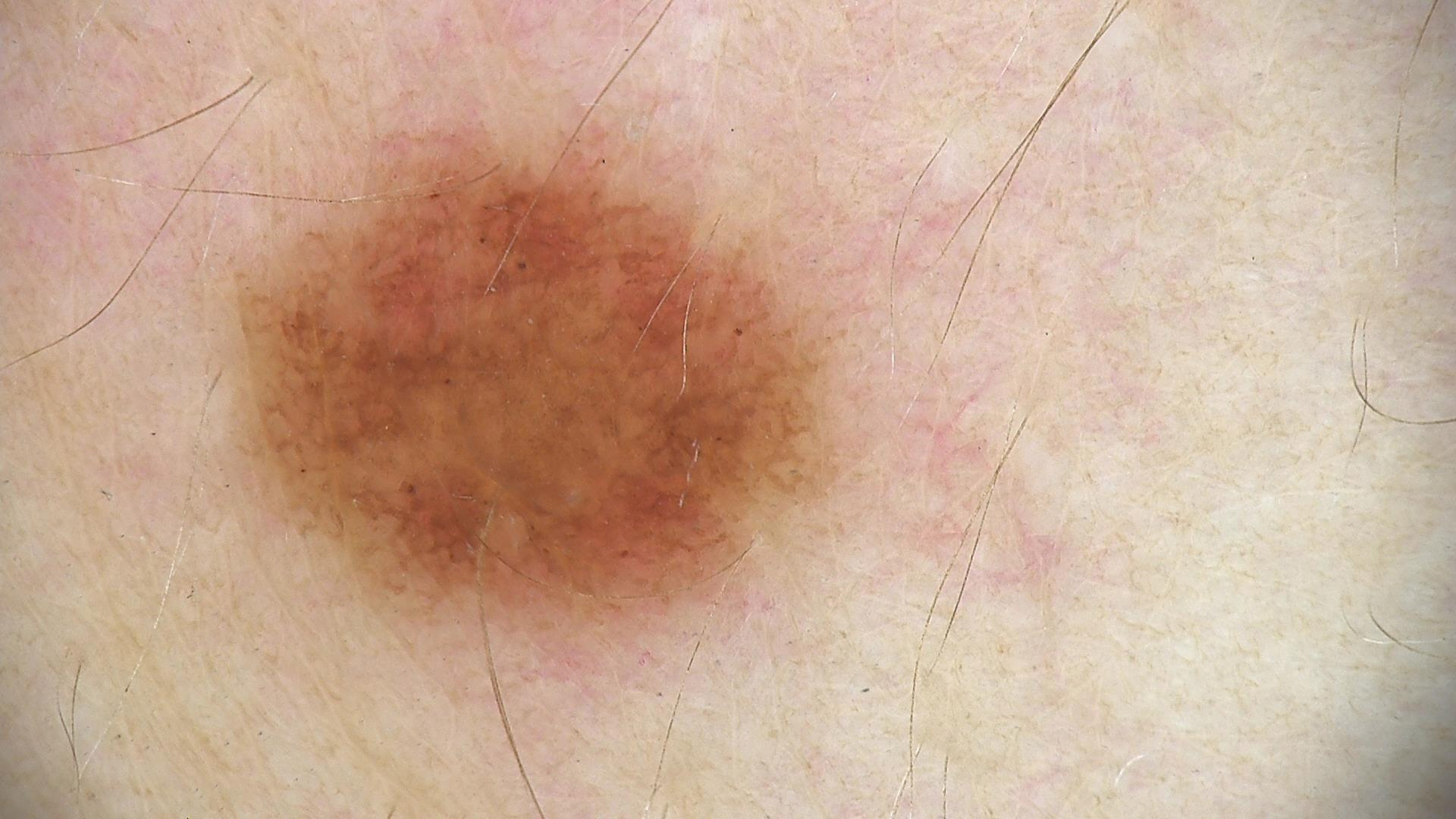Consistent with a dysplastic junctional nevus.